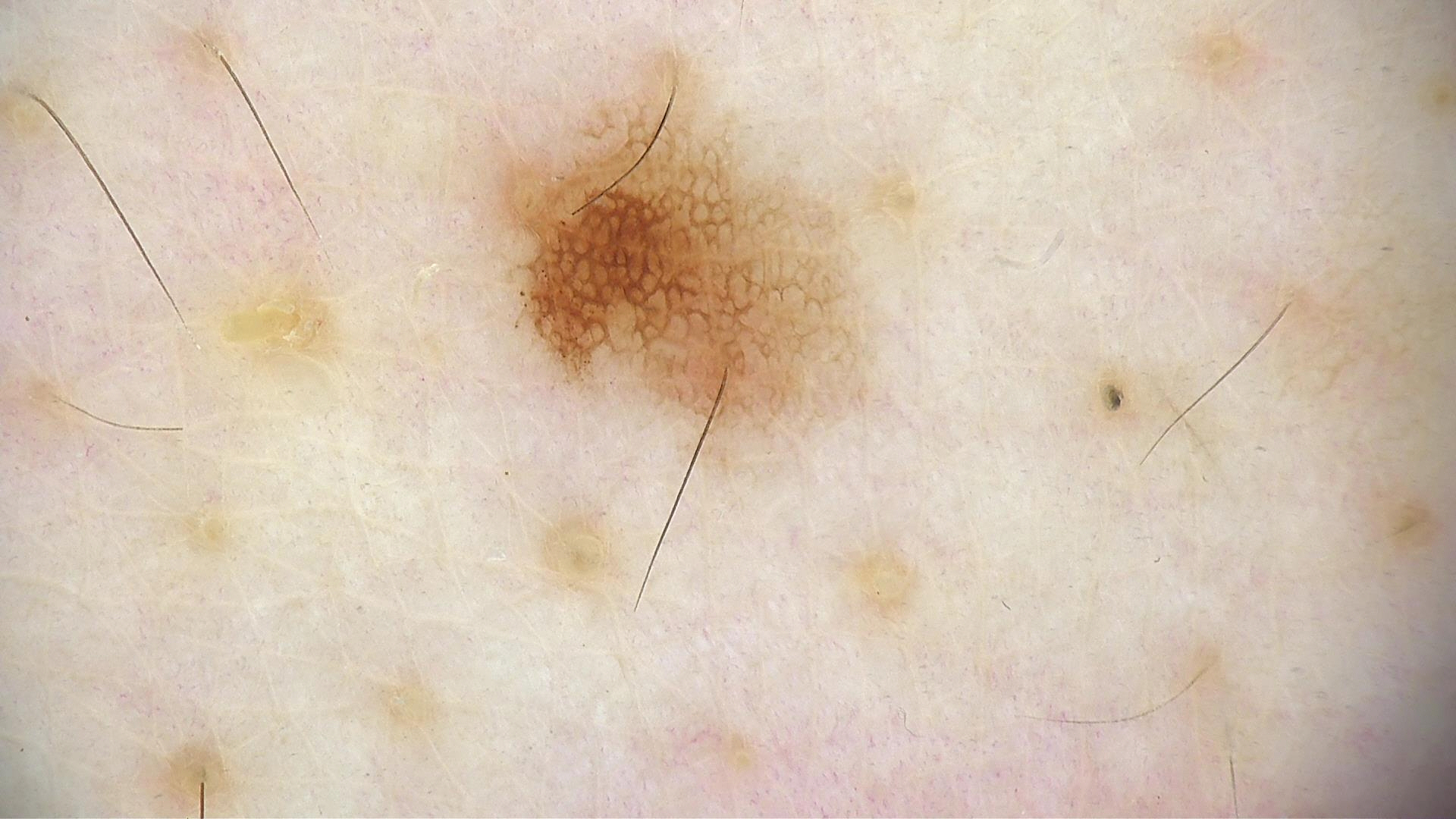Impression:
Classified as a dysplastic junctional nevus.